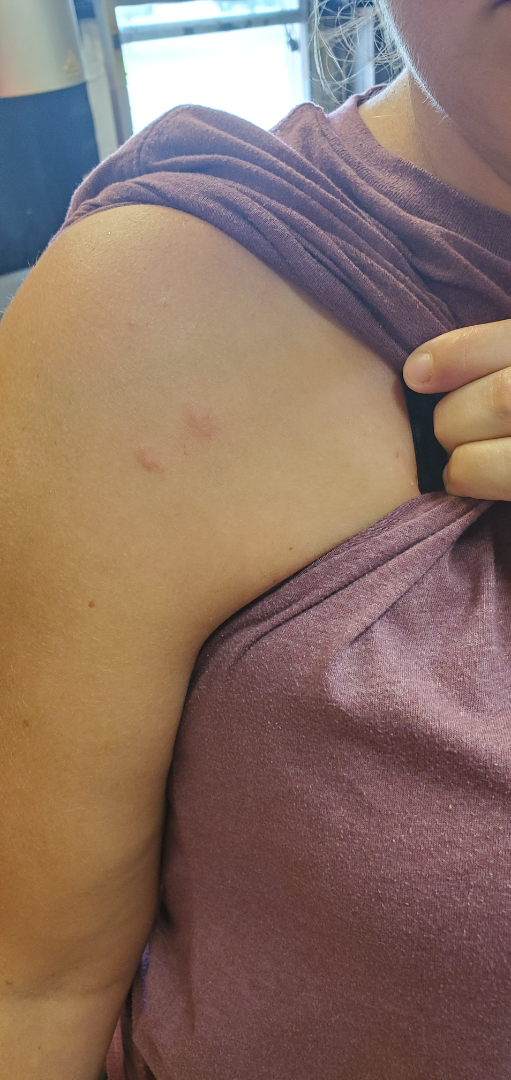Findings:
The reviewing dermatologist was unable to assign a differential diagnosis from the image.
Background:
The photo was captured at a distance.